A close-up photograph:
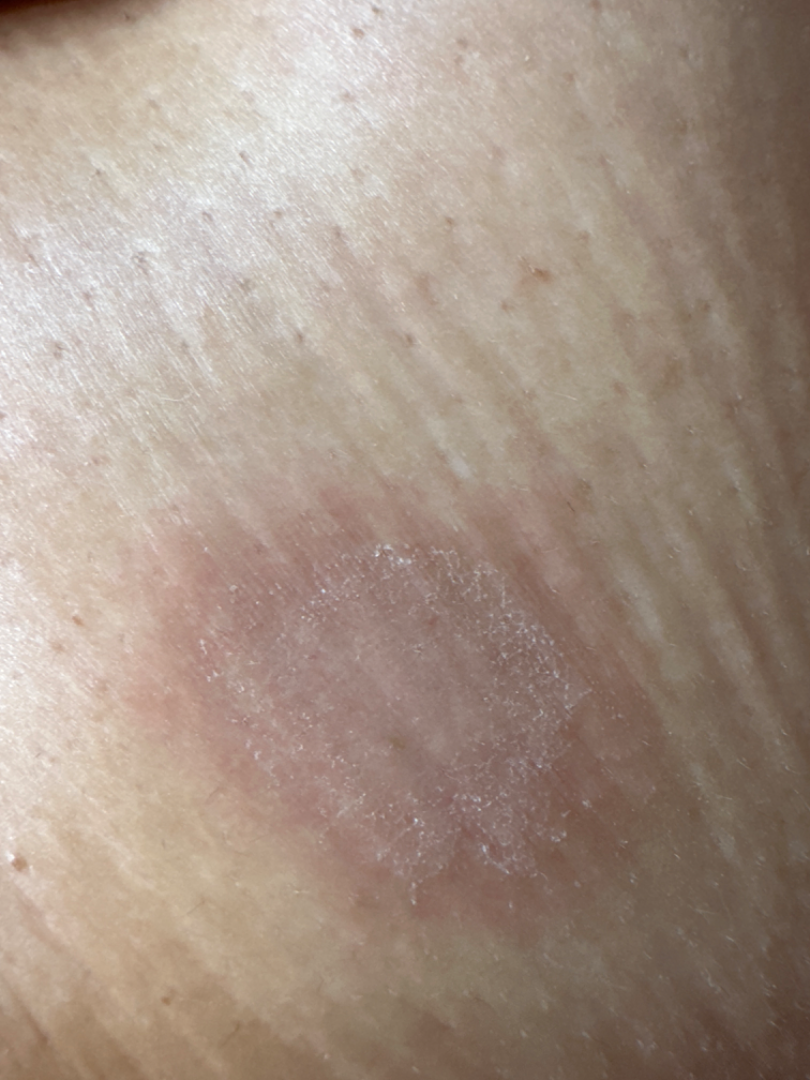Review: On photographic review: the leading impression is Pityriasis rosea.